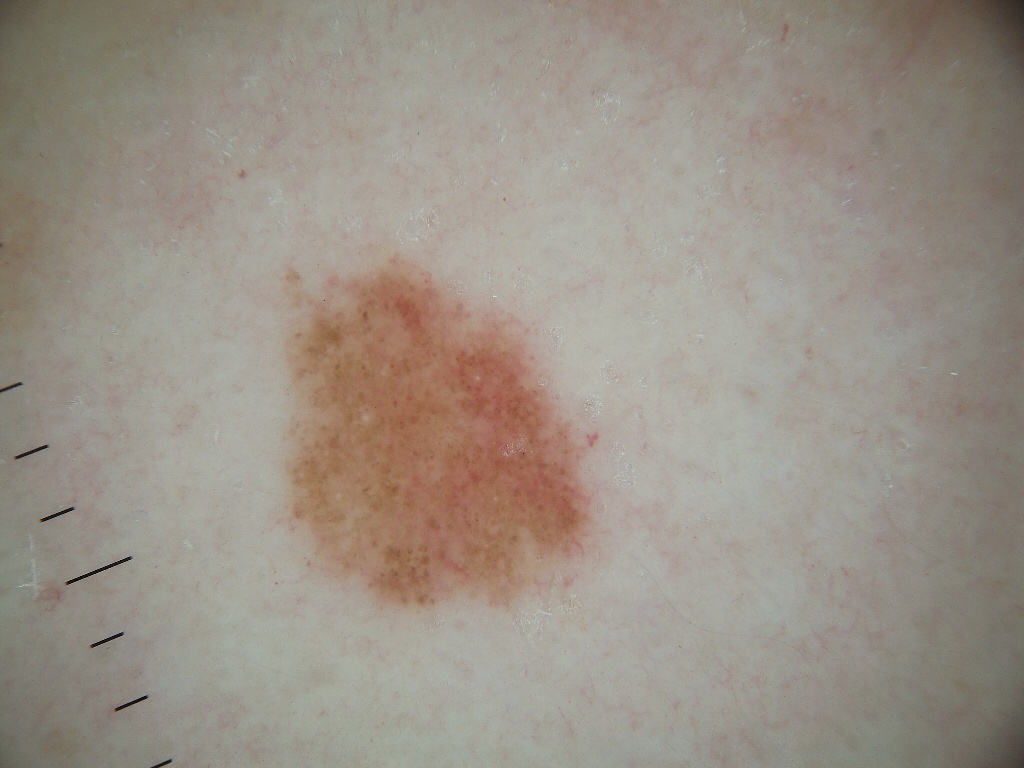imaging=dermoscopy of a skin lesion
patient=female, about 25 years old
lesion bbox=box(281, 253, 593, 611)
dermoscopic pattern=milia-like cysts and globules
assessment=a melanocytic nevus, a benign lesion